A dermoscopy image of a single skin lesion.
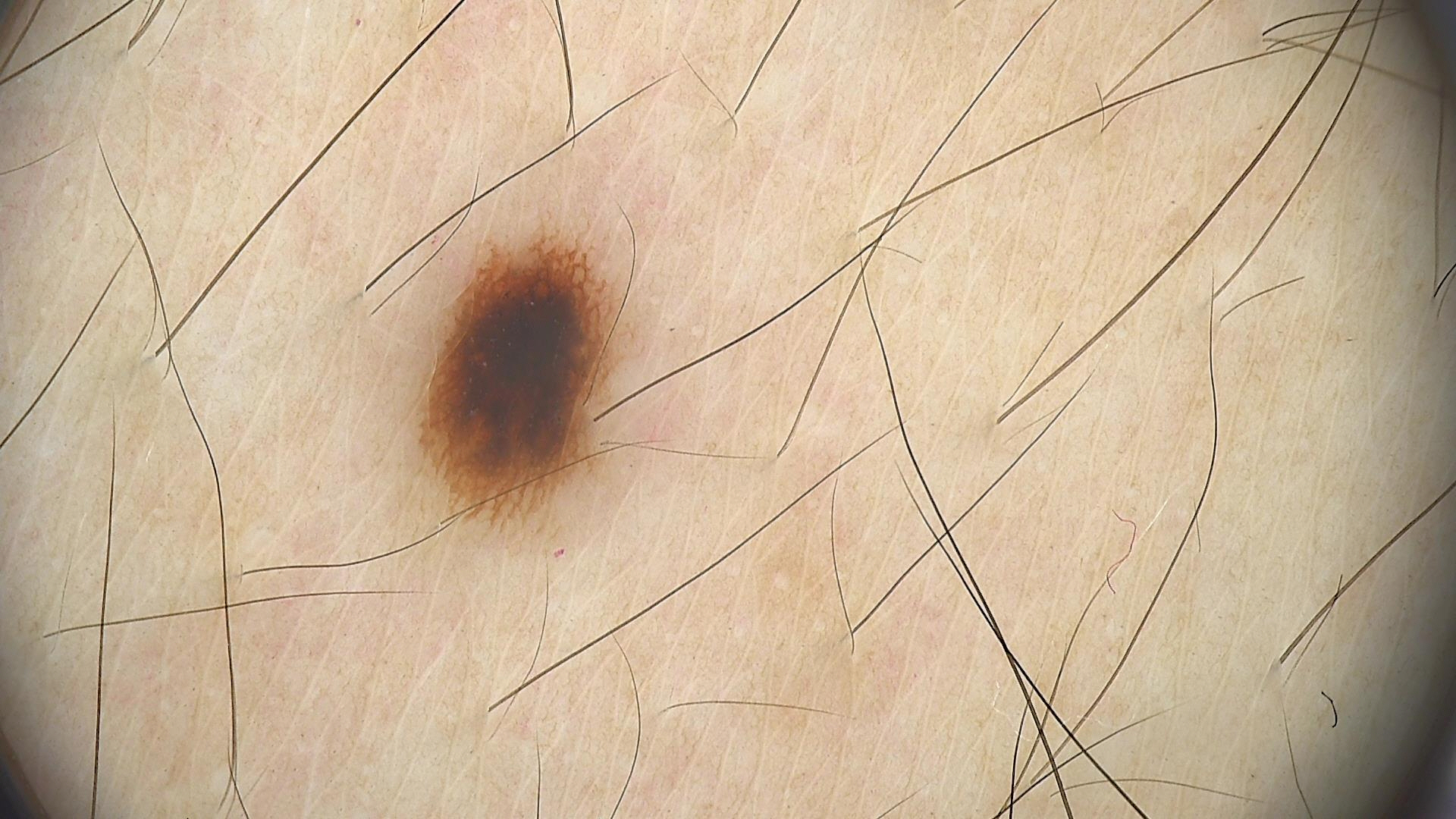assessment — dysplastic junctional nevus (expert consensus).